Texture is reported as raised or bumpy, the lesion involves the leg, an image taken at an angle, Fitzpatrick phototype III — 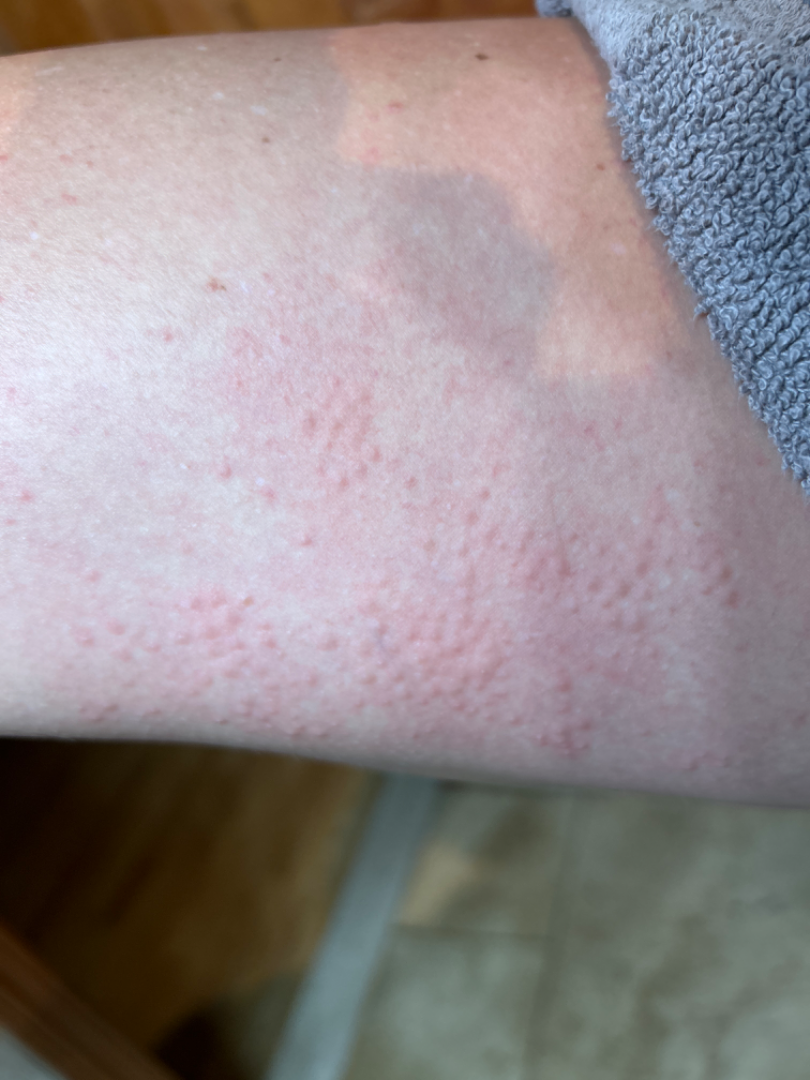On dermatologist assessment of the image, most consistent with Eczema.